A dermatoscopic image of a skin lesion.
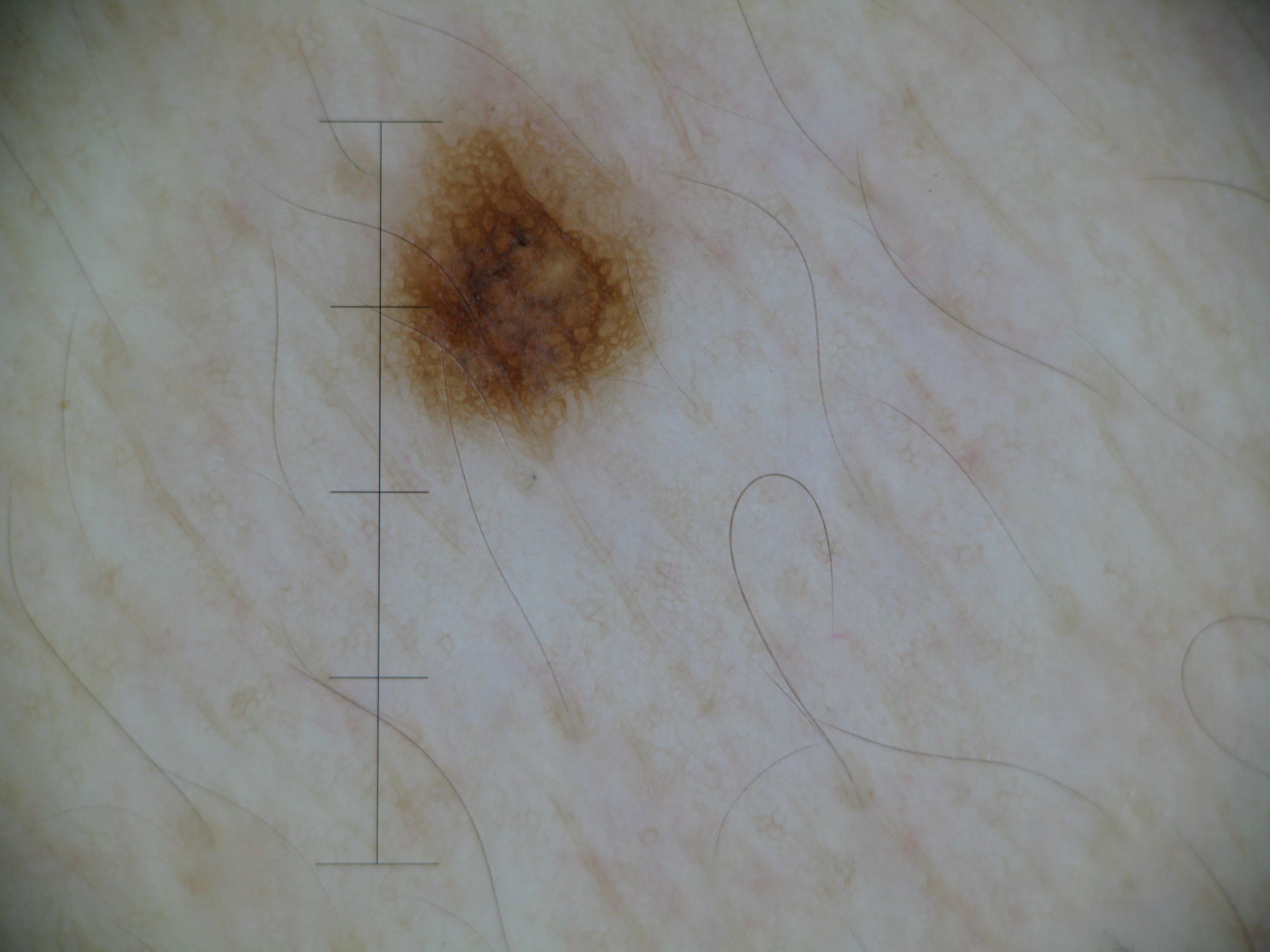The diagnosis was a dysplastic junctional nevus.